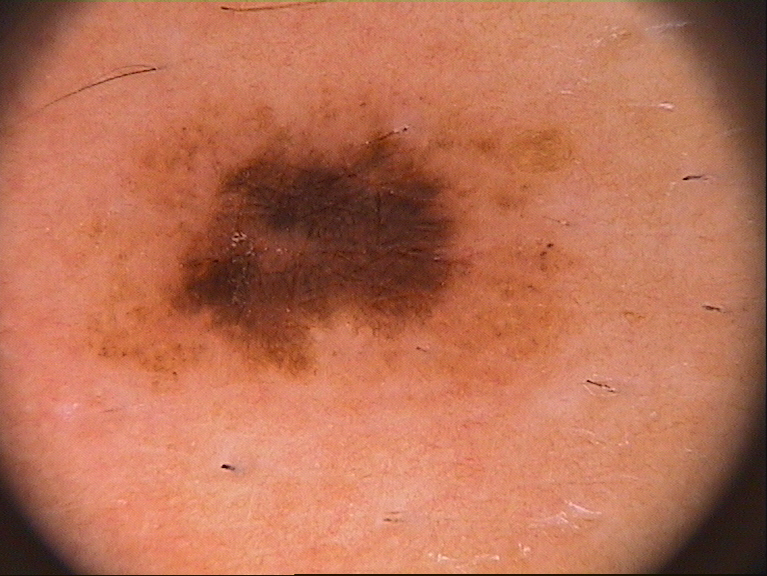The patient is a male aged 33-37.
A dermoscopic close-up of a skin lesion.
As (left, top, right, bottom), the lesion is located at bbox(77, 85, 588, 395).
On dermoscopy, the lesion shows pigment network and globules.
The lesion was assessed as a melanocytic nevus, a benign lesion.